A clinical photo of a skin lesion taken with a smartphone · a subject 57 years old — 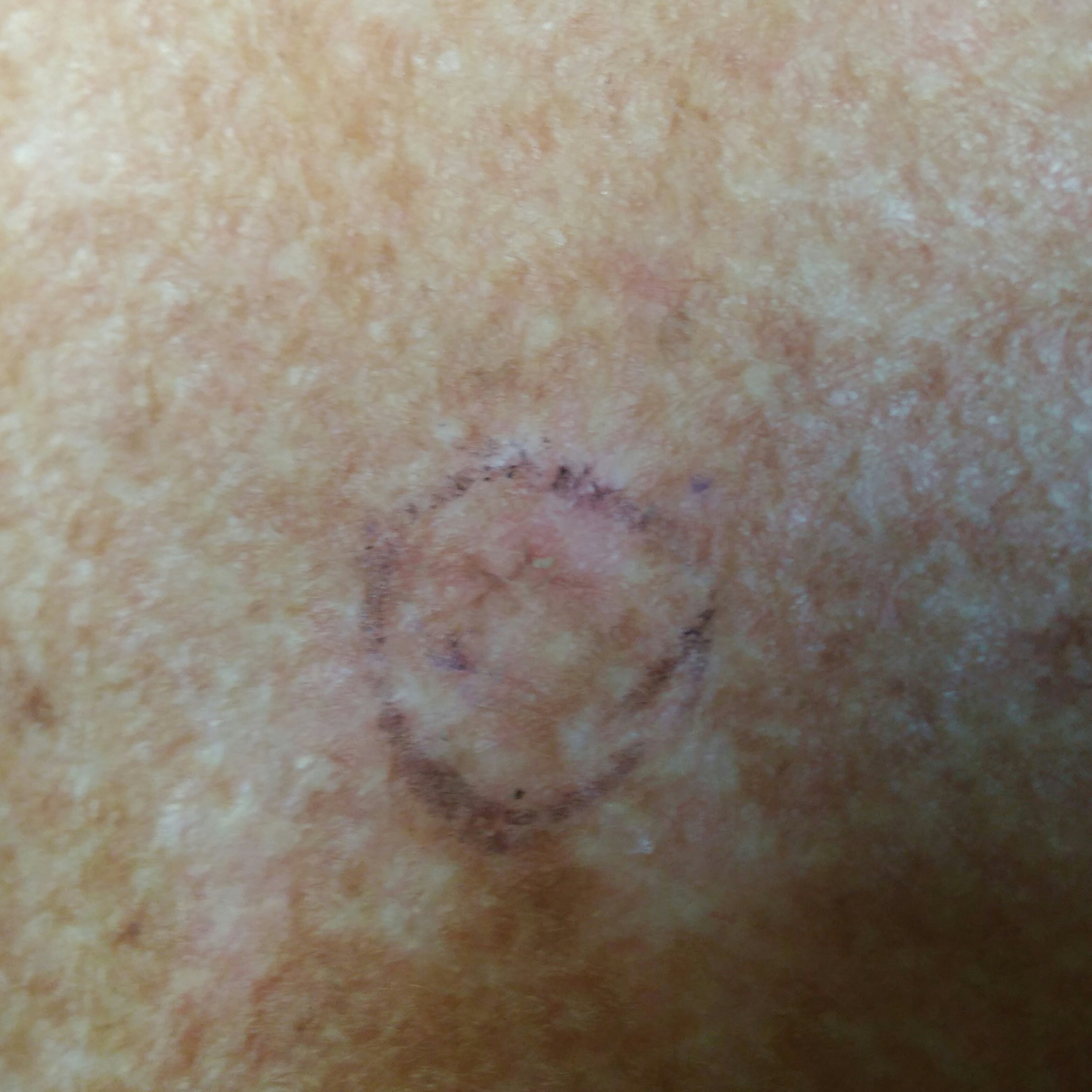The lesion is located on the chest. The patient describes that the lesion itches. Expert review favored a lesion of indeterminate malignant potential — an actinic keratosis.